This image was taken at an angle: 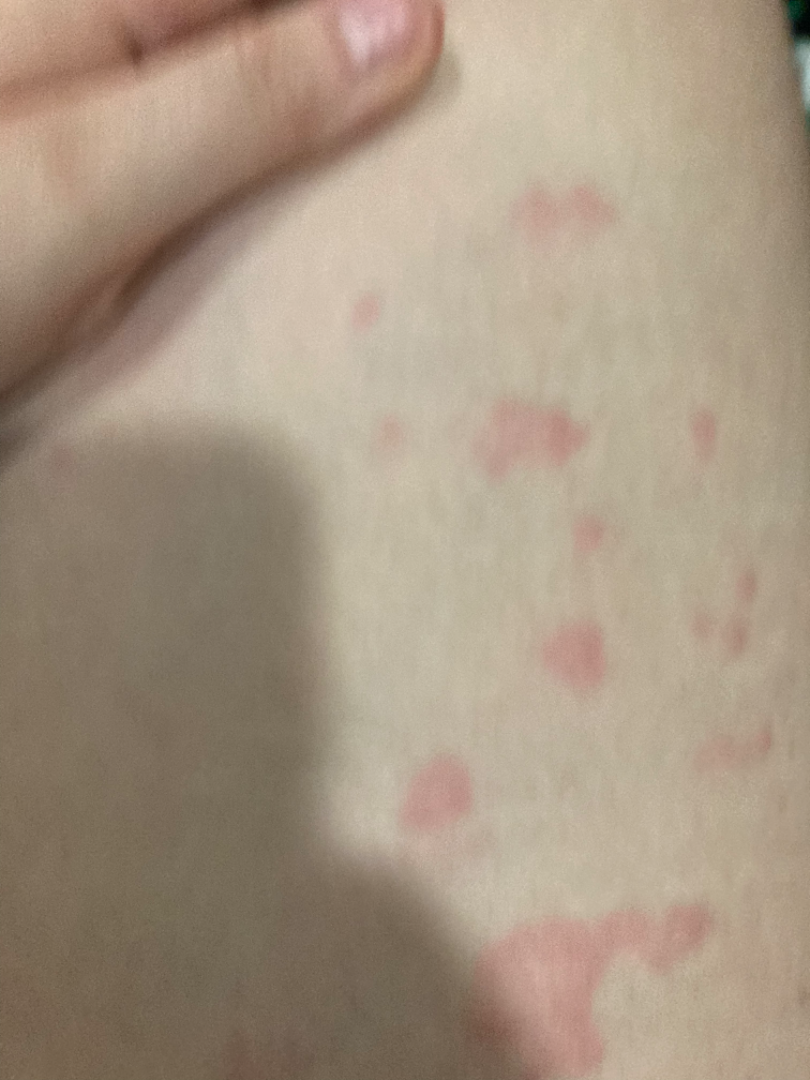On dermatologist assessment of the image, most consistent with Urticaria.